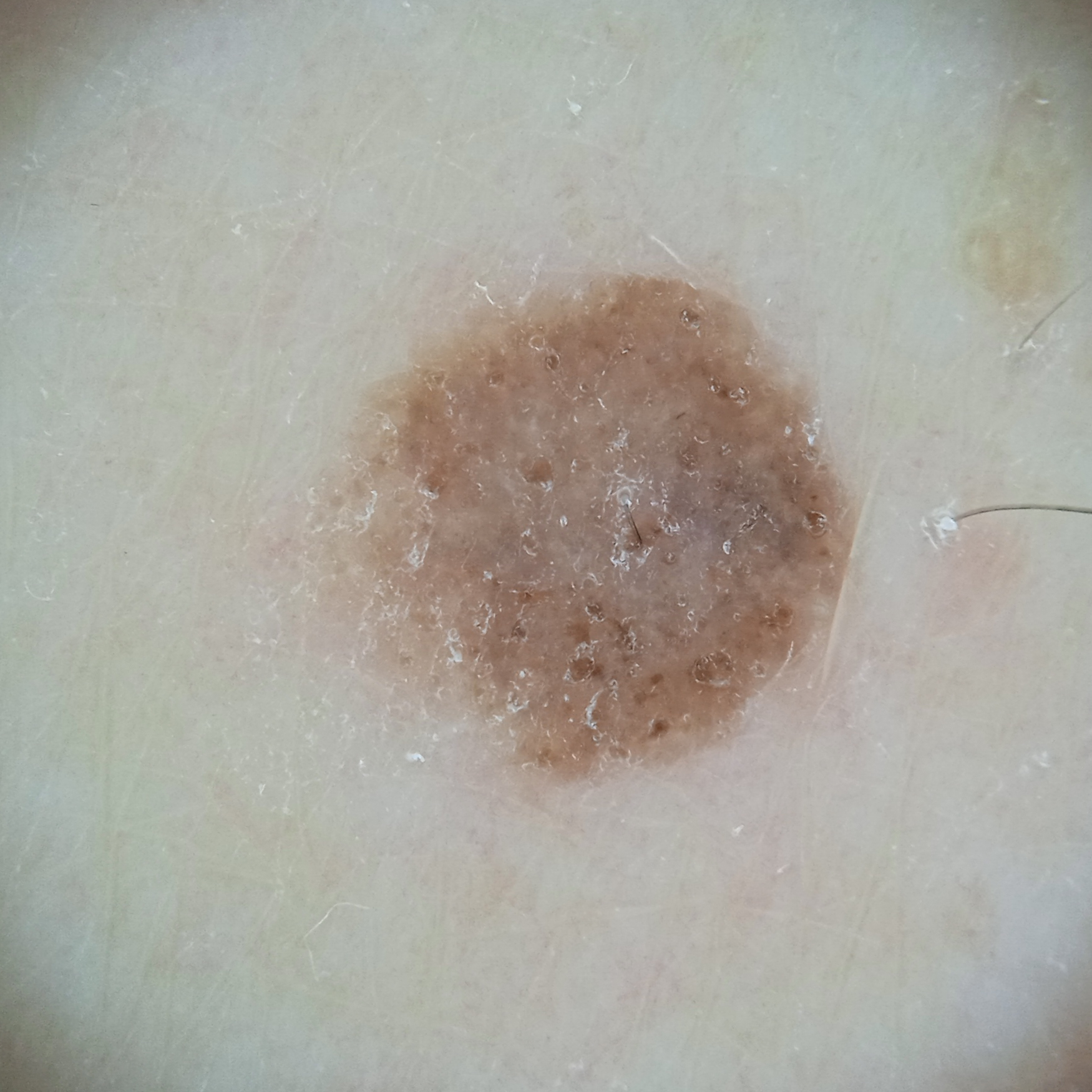Case summary:
A dermatoscopic image of a skin lesion. The patient describes having few moles overall. Collected as part of a research study, without a referral diagnosis. The patient says their skin tans without first burning. A male patient age 79.
Conclusion:
The dermatologists' assessment was a melanocytic nevus.